A patient in their late 30s.
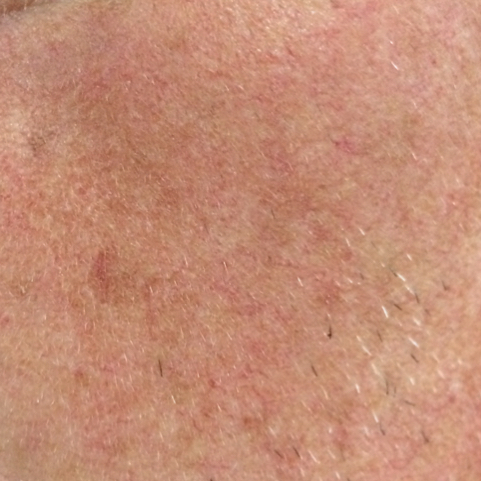Located on the face.
The consensus clinical diagnosis was an actinic keratosis.